A skin lesion imaged with contact-polarized dermoscopy. A female patient approximately 20 years of age.
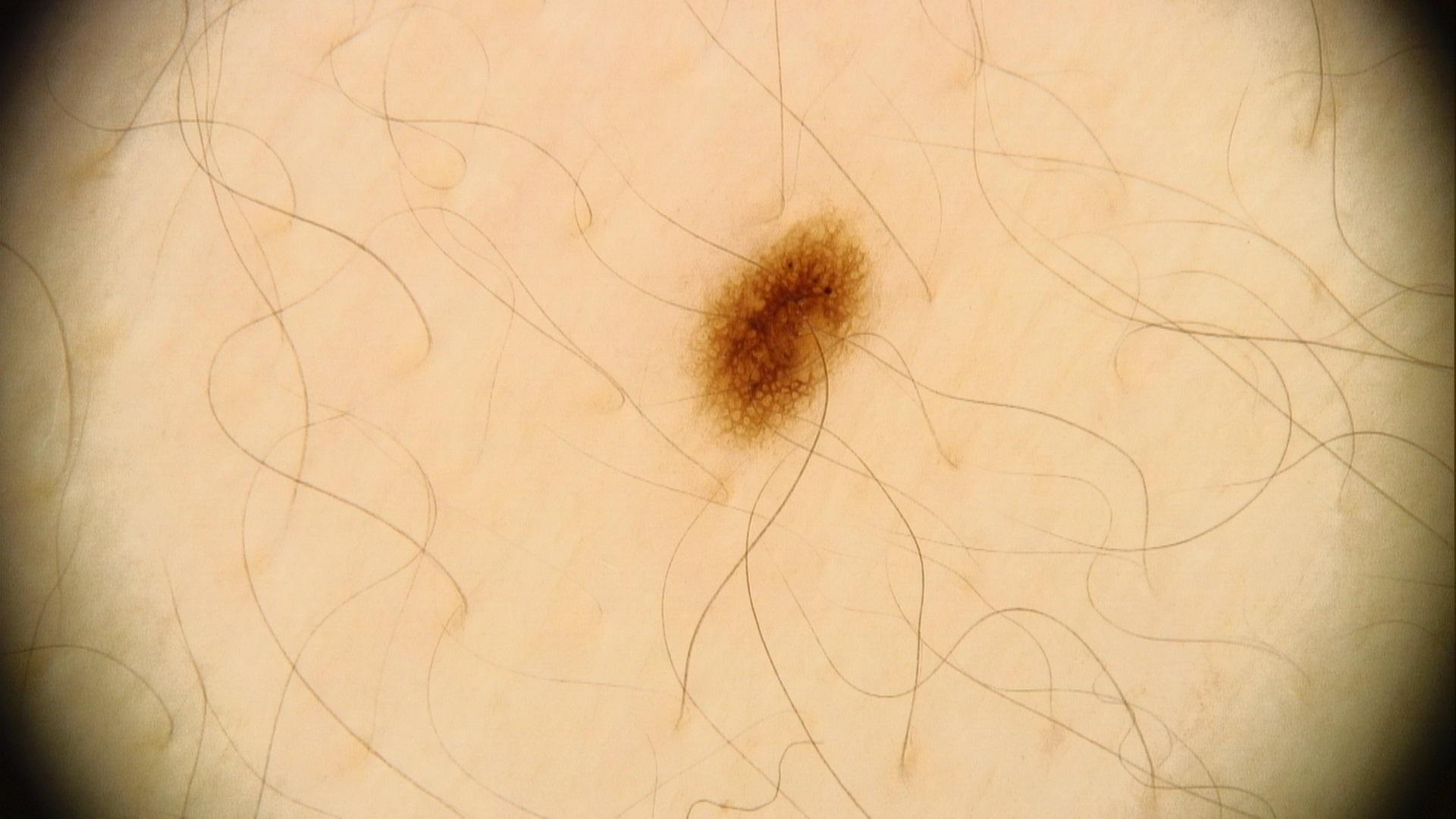Notes:
– body site: the trunk
– impression: Nevus